The patient says their skin reddens with sun exposure; acquired for a research image collection, with no referral diagnosis; a clinical photograph of a skin lesion; on a questionnaire the patient reported a personal history of cancer, a family history of skin cancer, and a personal history of skin cancer; a female patient 54 years of age; the patient describes having numerous moles: 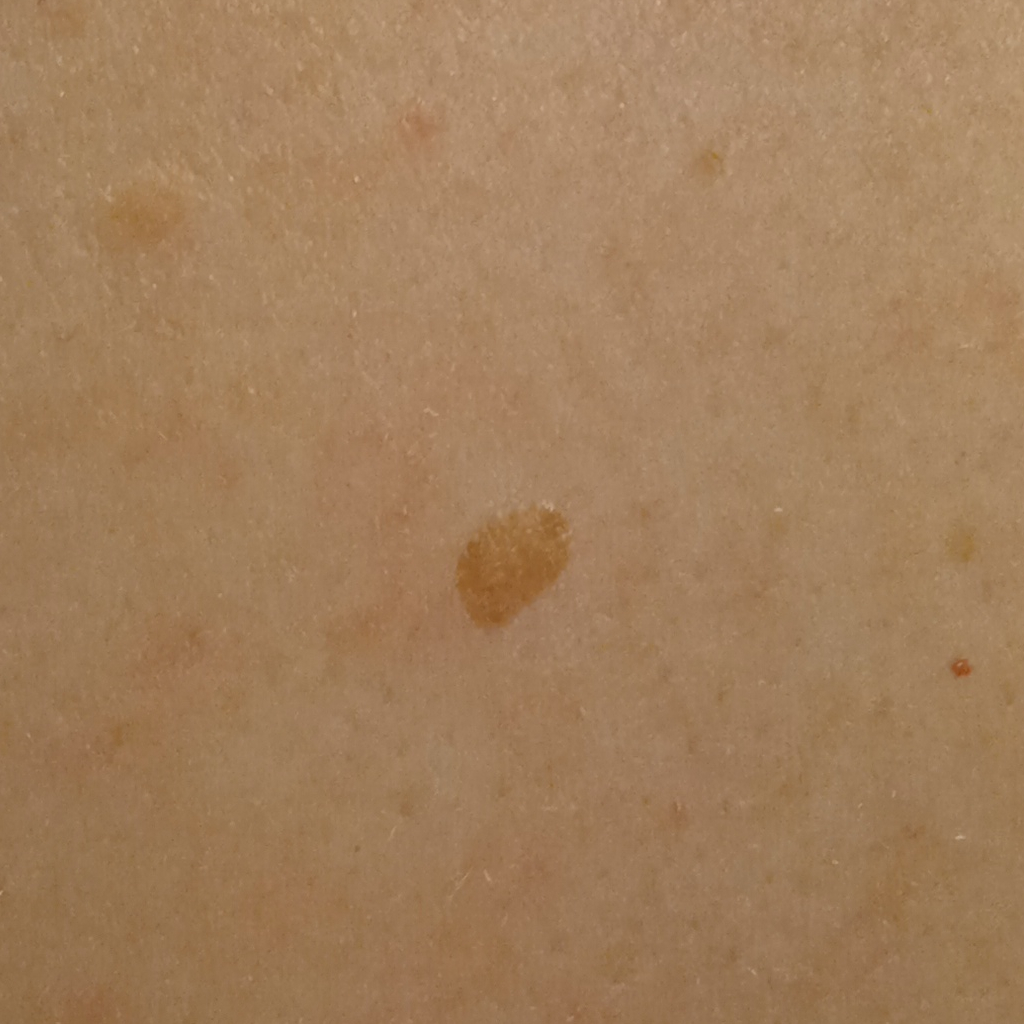Summary:
Located on the back. The lesion is about 5.5 mm across.
Impression:
Dermatologist review favored a seborrheic keratosis.